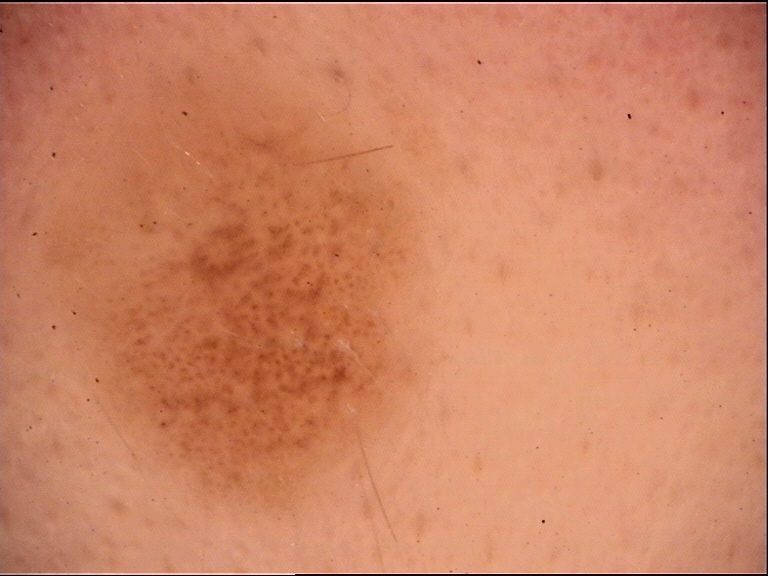Labeled as a dysplastic junctional nevus.